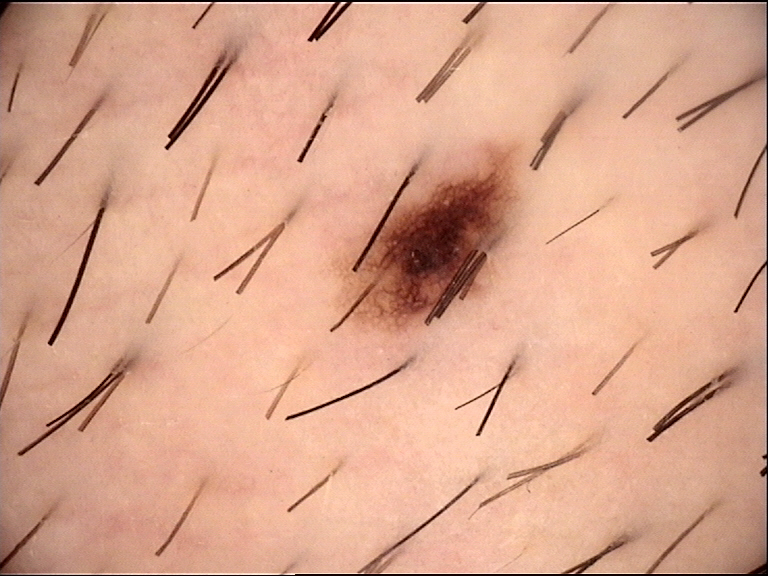Case:
A dermoscopy image of a single skin lesion.
Conclusion:
Labeled as a dysplastic junctional nevus.